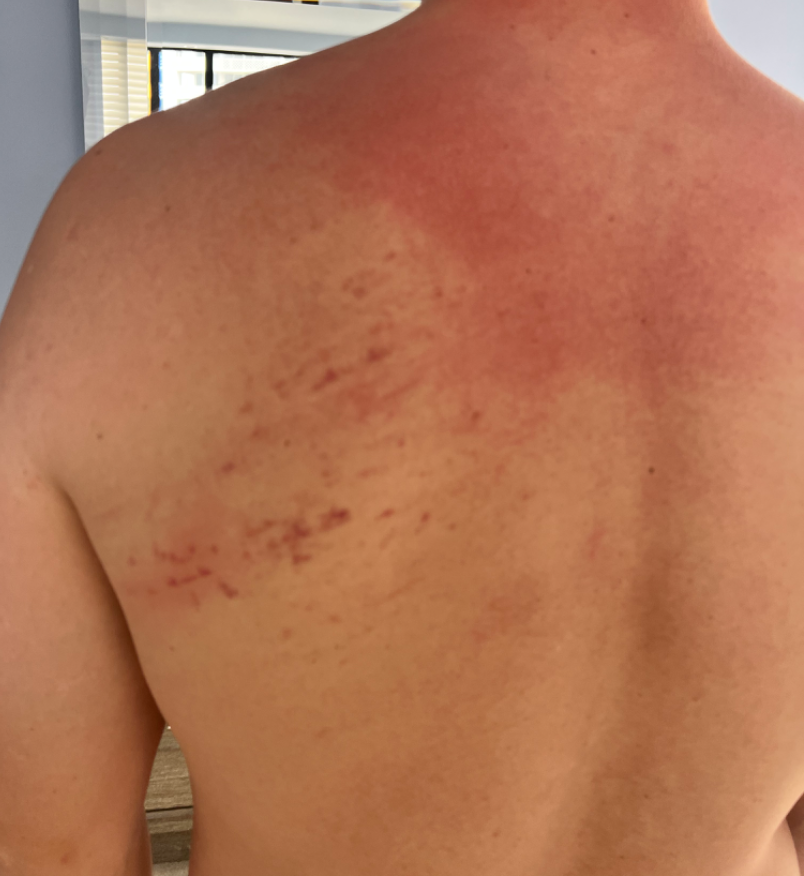Findings:
The reviewer was unable to grade this case for skin condition.
Background:
The lesion involves the back of the torso. Reported lesion symptoms include darkening. The patient notes the lesion is flat. A close-up photograph. The patient considered this skin that appeared healthy to them.